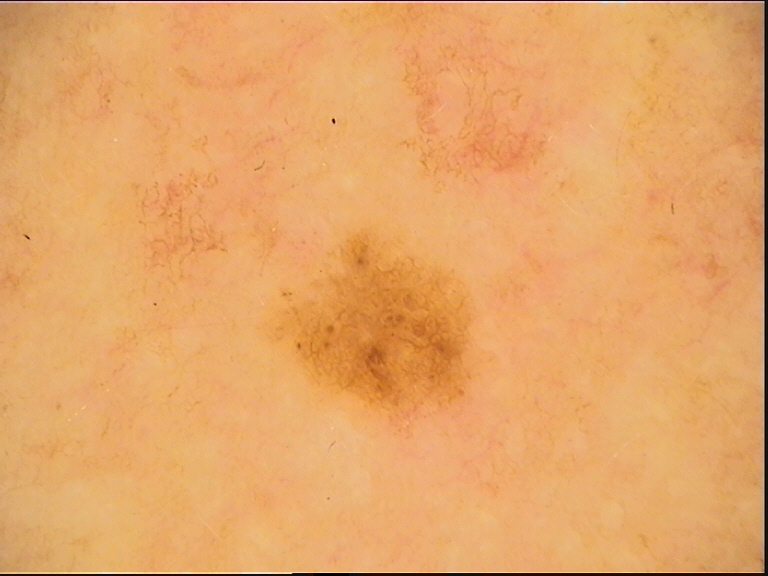imaging=dermatoscopy
assessment=dysplastic junctional nevus (expert consensus)